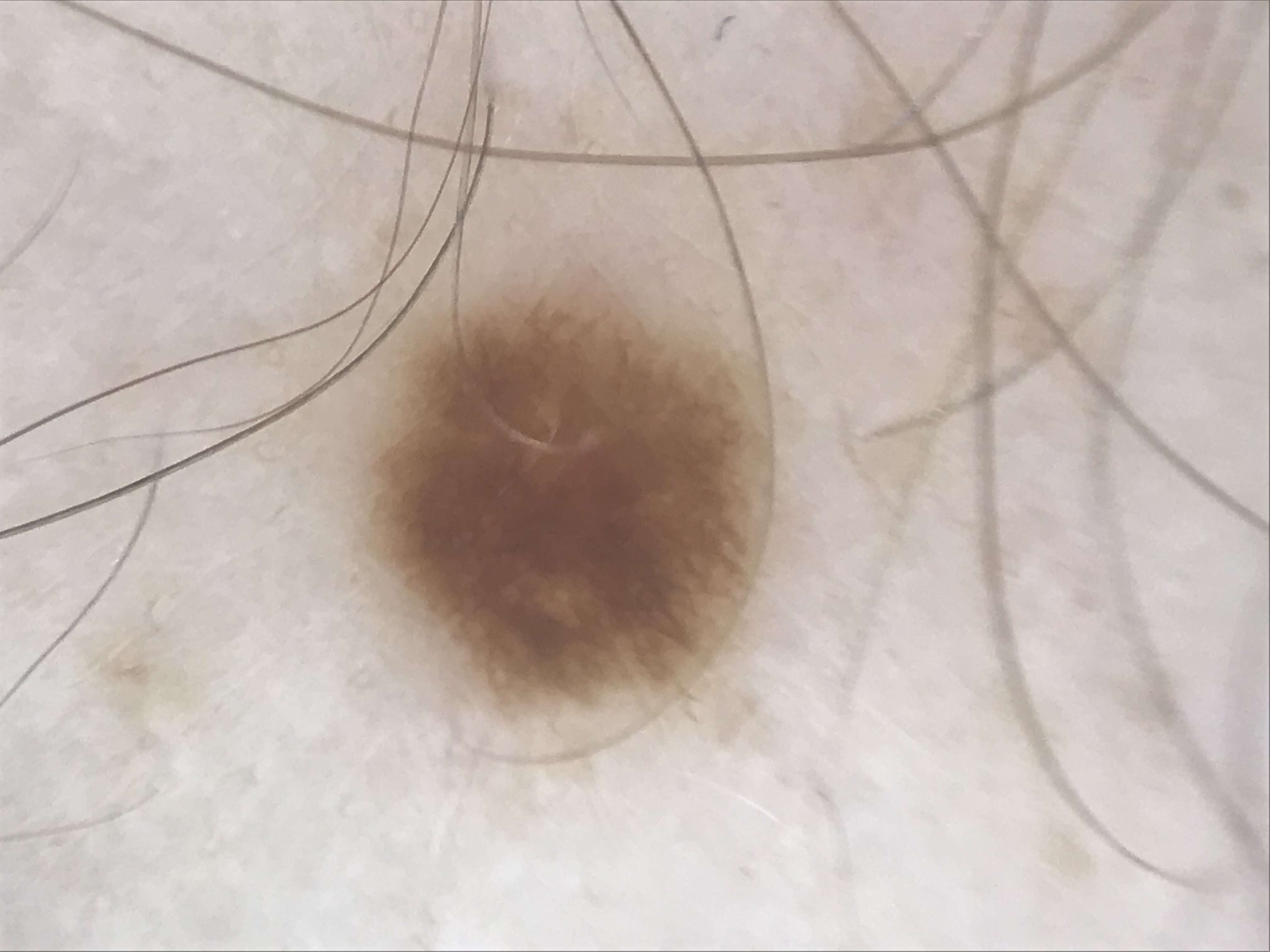Q: How is the lesion classified?
A: banal
Q: What was the diagnostic impression?
A: junctional nevus (expert consensus)